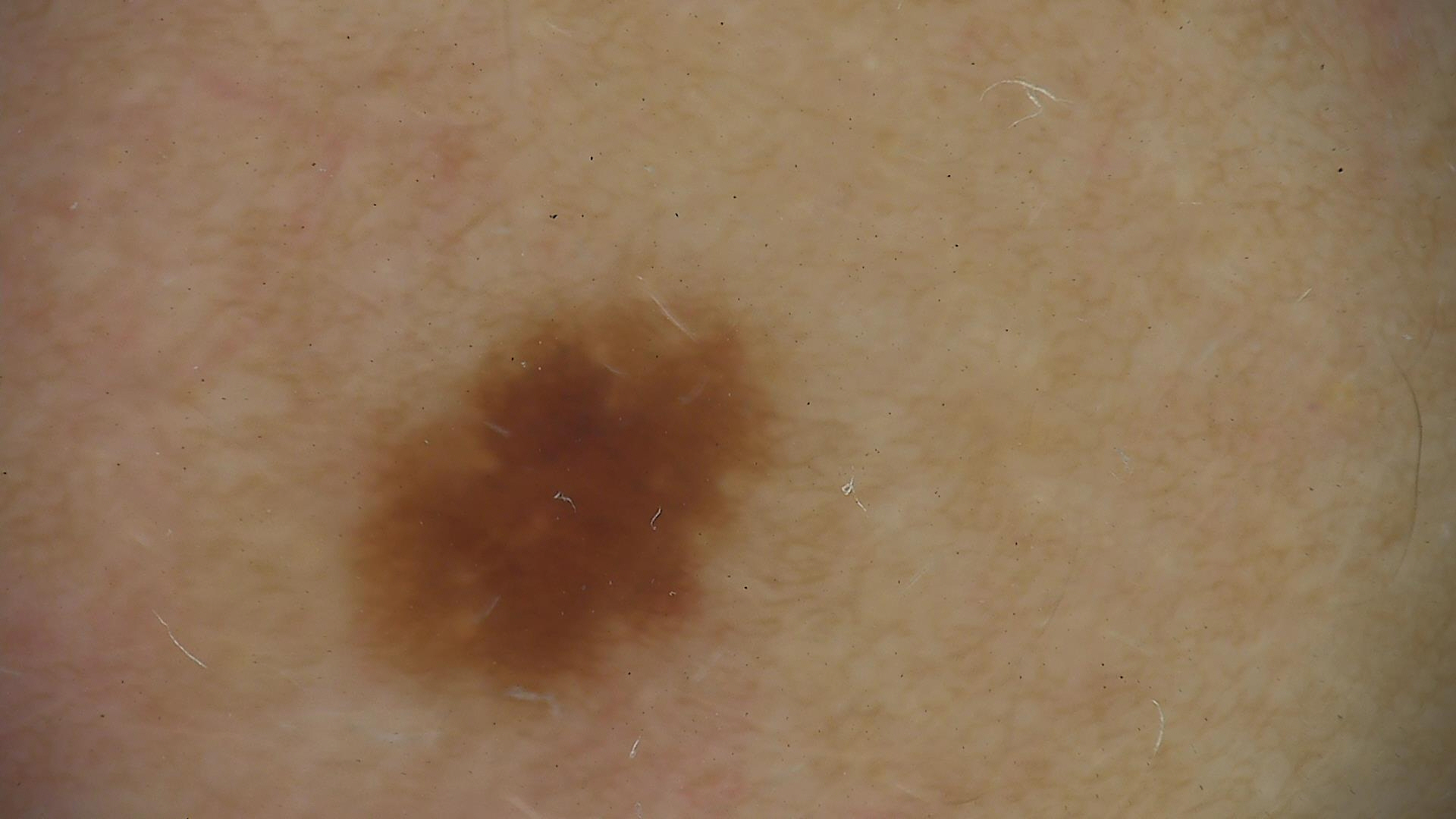  image: dermoscopy
  diagnosis:
    name: dysplastic junctional nevus
    code: jd
    malignancy: benign
    super_class: melanocytic
    confirmation: expert consensus